Close-up view:
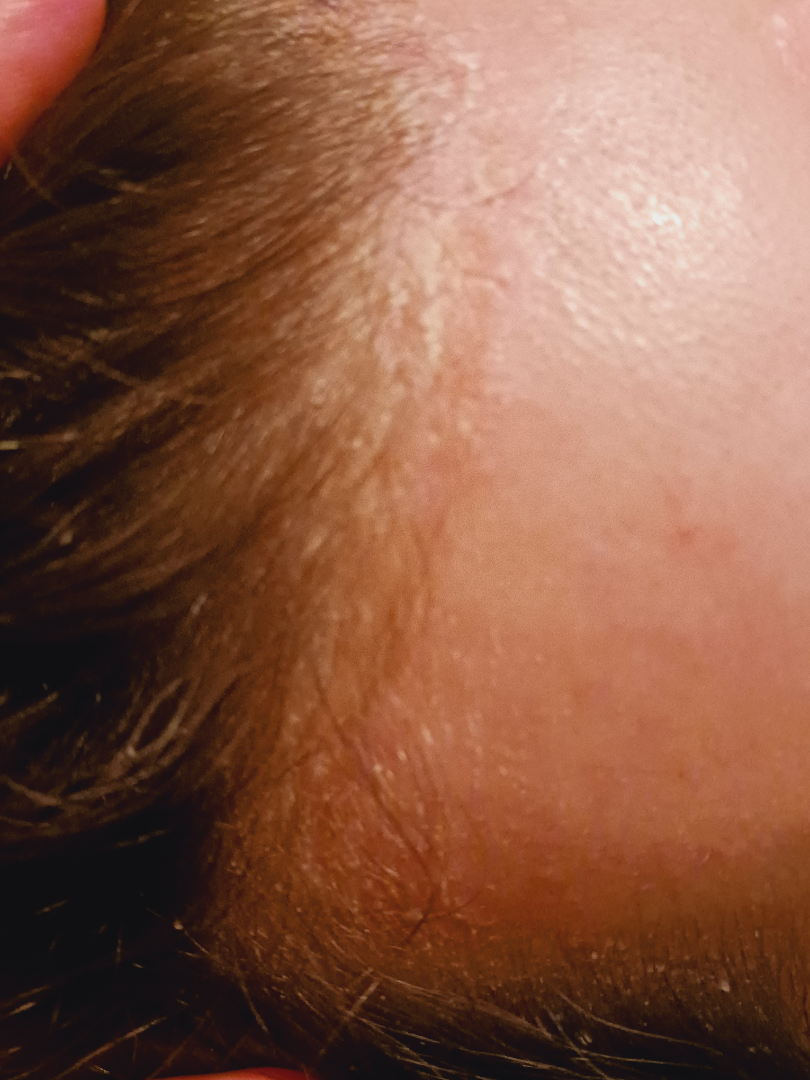On teledermatology review: consistent with Seborrheic Dermatitis.